A female patient 59 years old — 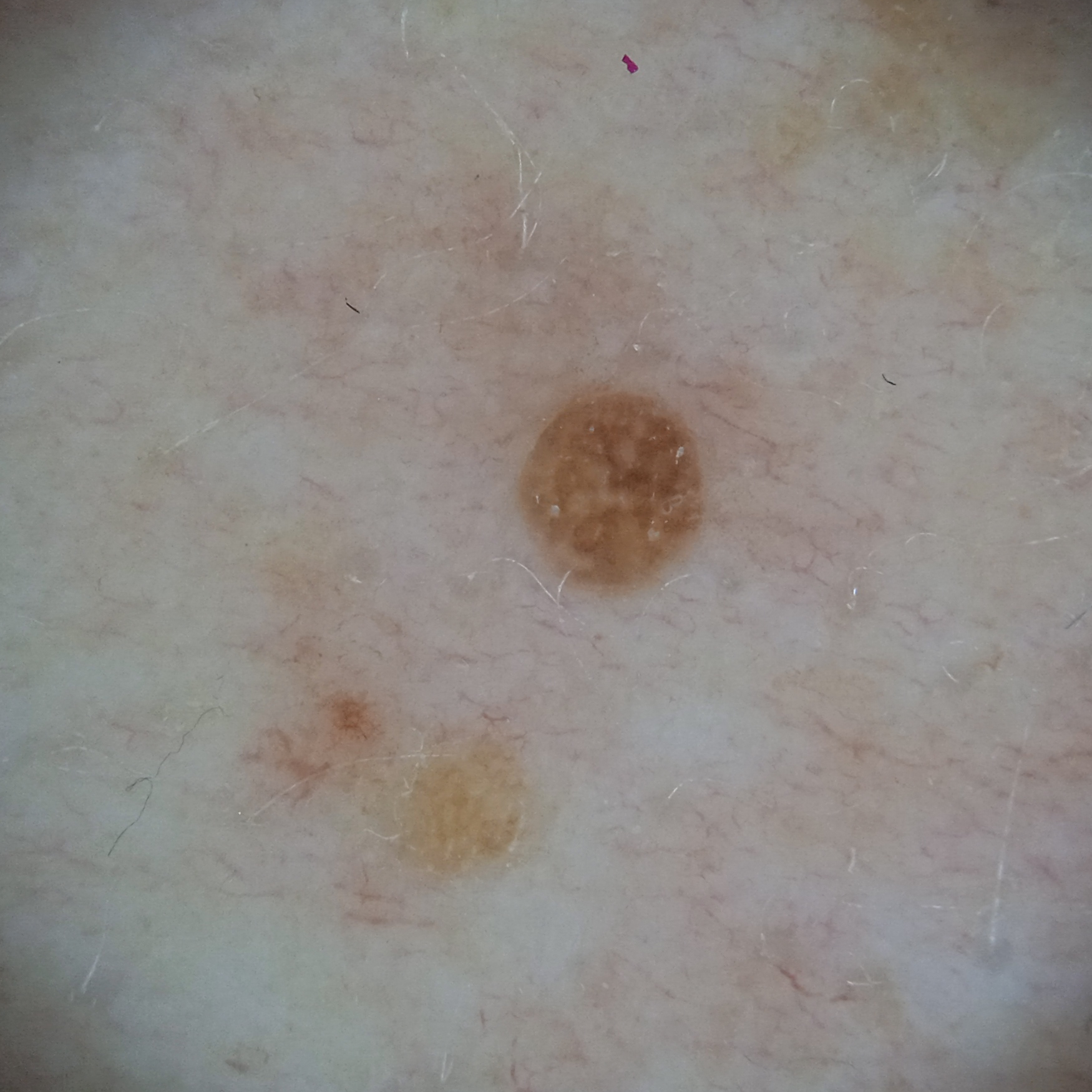<case>
  <lesion_location>the torso</lesion_location>
  <lesion_size>
    <diameter_mm>2.2</diameter_mm>
  </lesion_size>
  <diagnosis>
    <name>seborrheic keratosis</name>
    <malignancy>benign</malignancy>
  </diagnosis>
</case>